A clinical photo of a skin lesion taken with a smartphone:
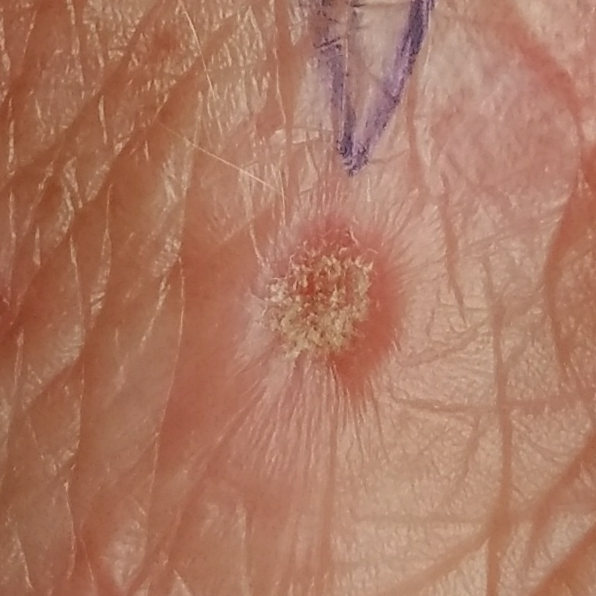The lesion involves a hand.
The patient reports that the lesion is elevated, but has not bled.
Diagnosed by dermatologist consensus as an actinic keratosis.